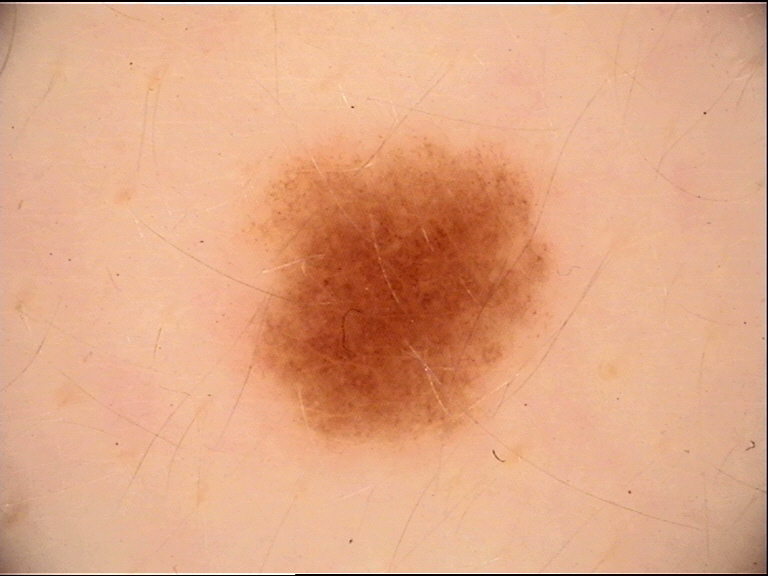imaging = dermoscopy
diagnostic label = dysplastic junctional nevus (expert consensus)